Dermoscopy of a skin lesion.
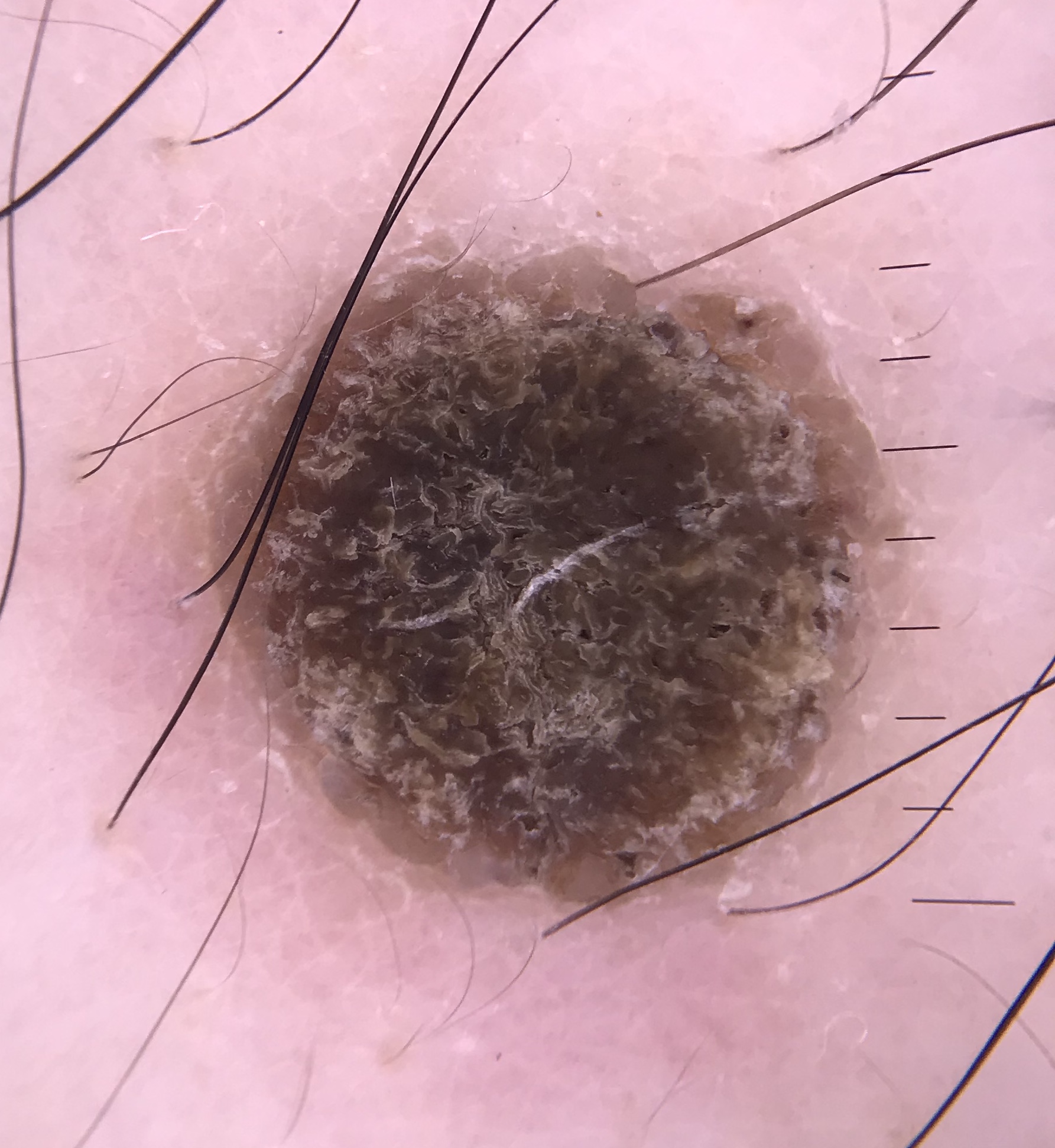class: seborrheic keratosis (expert consensus).